Dermoscopy of a skin lesion:
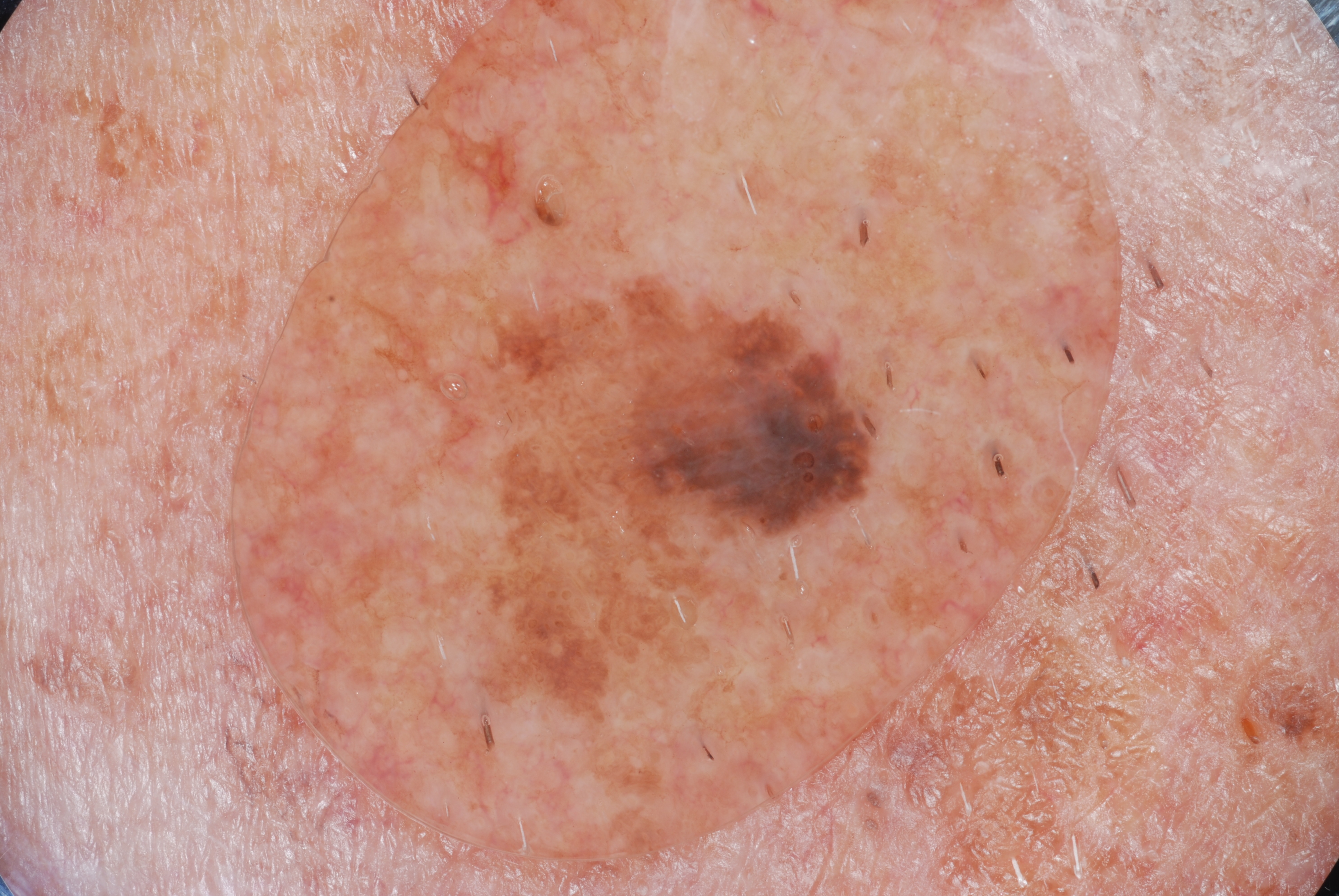The visible lesion spans 455, 269, 889, 725.
On dermoscopy, the lesion shows milia-like cysts.
The lesion takes up about 12% of the image.
The clinical diagnosis was a seborrheic keratosis, a keratinocytic lesion.